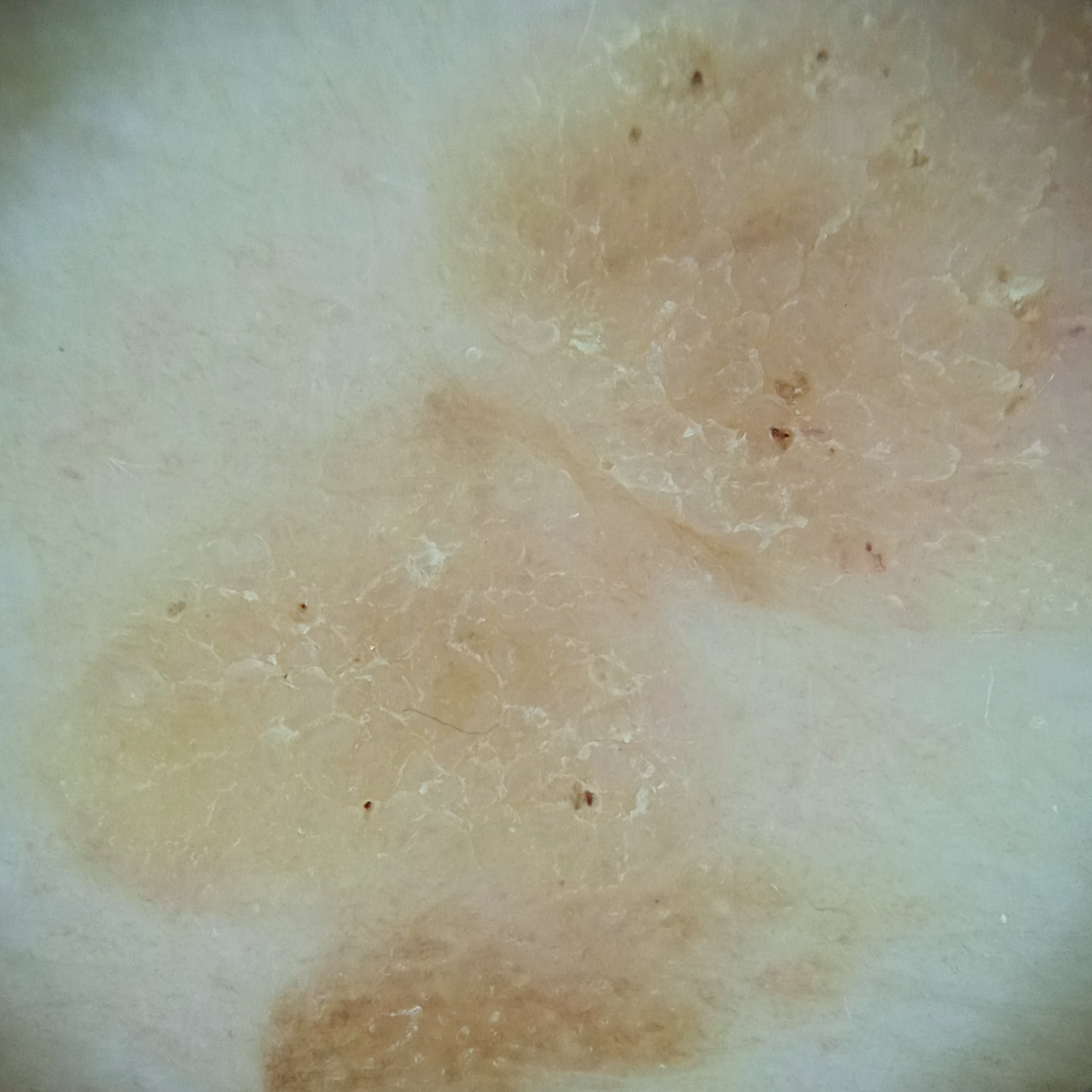A female patient 81 years of age. A dermatoscopic image of a skin lesion. Imaged for a research study, with no referral diagnosis recorded. The lesion is on the back. The lesion measures approximately 15.5 mm. The consensus diagnosis for this lesion was a seborrheic keratosis.